A dermatoscopic image of a skin lesion.
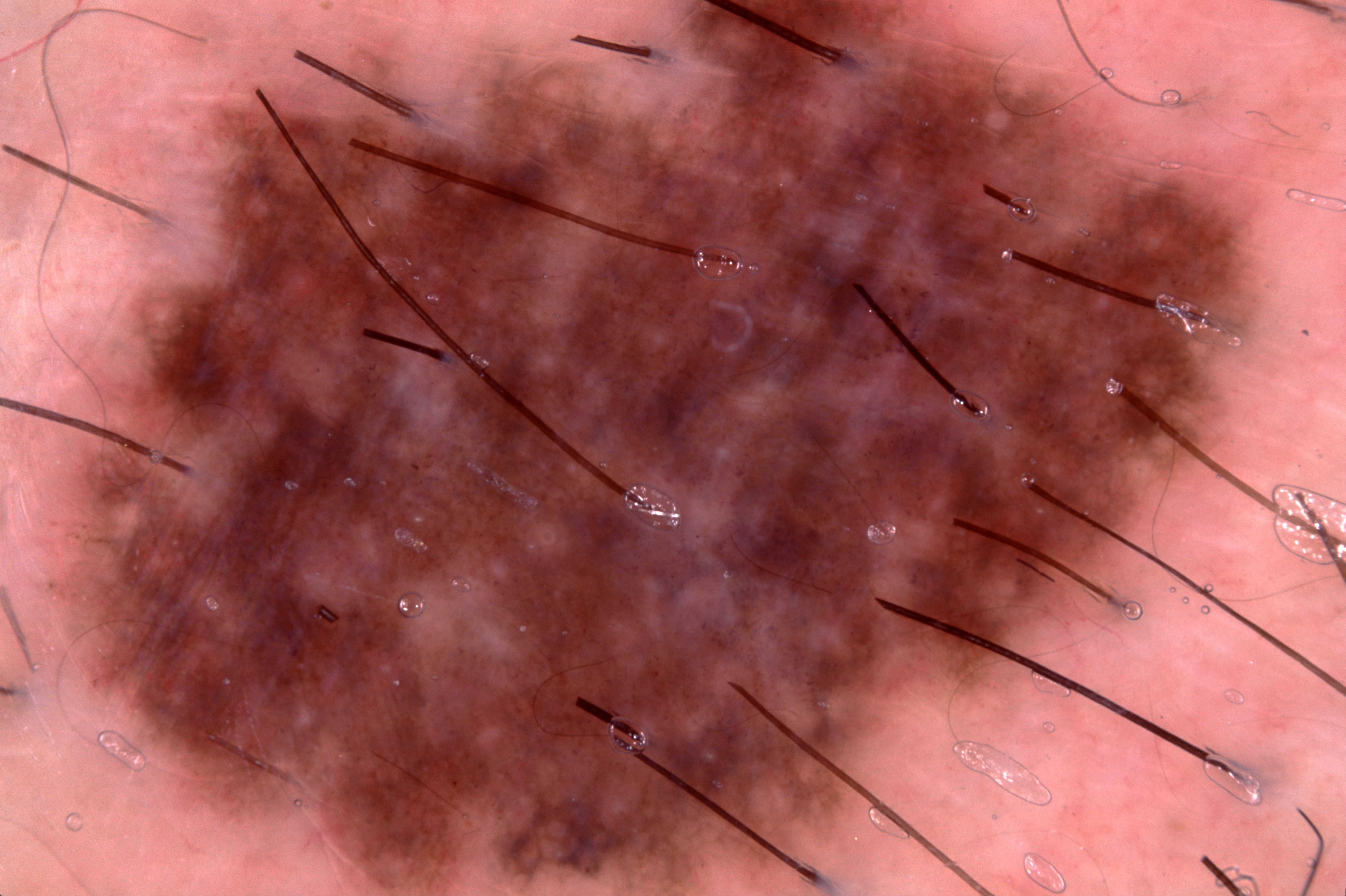The lesion extends across almost the whole field of view. Dermoscopic review identifies pigment network. The diagnostic assessment was a melanocytic nevus, a benign lesion.